A male subject, aged approximately 35 · a dermoscopic view of a skin lesion.
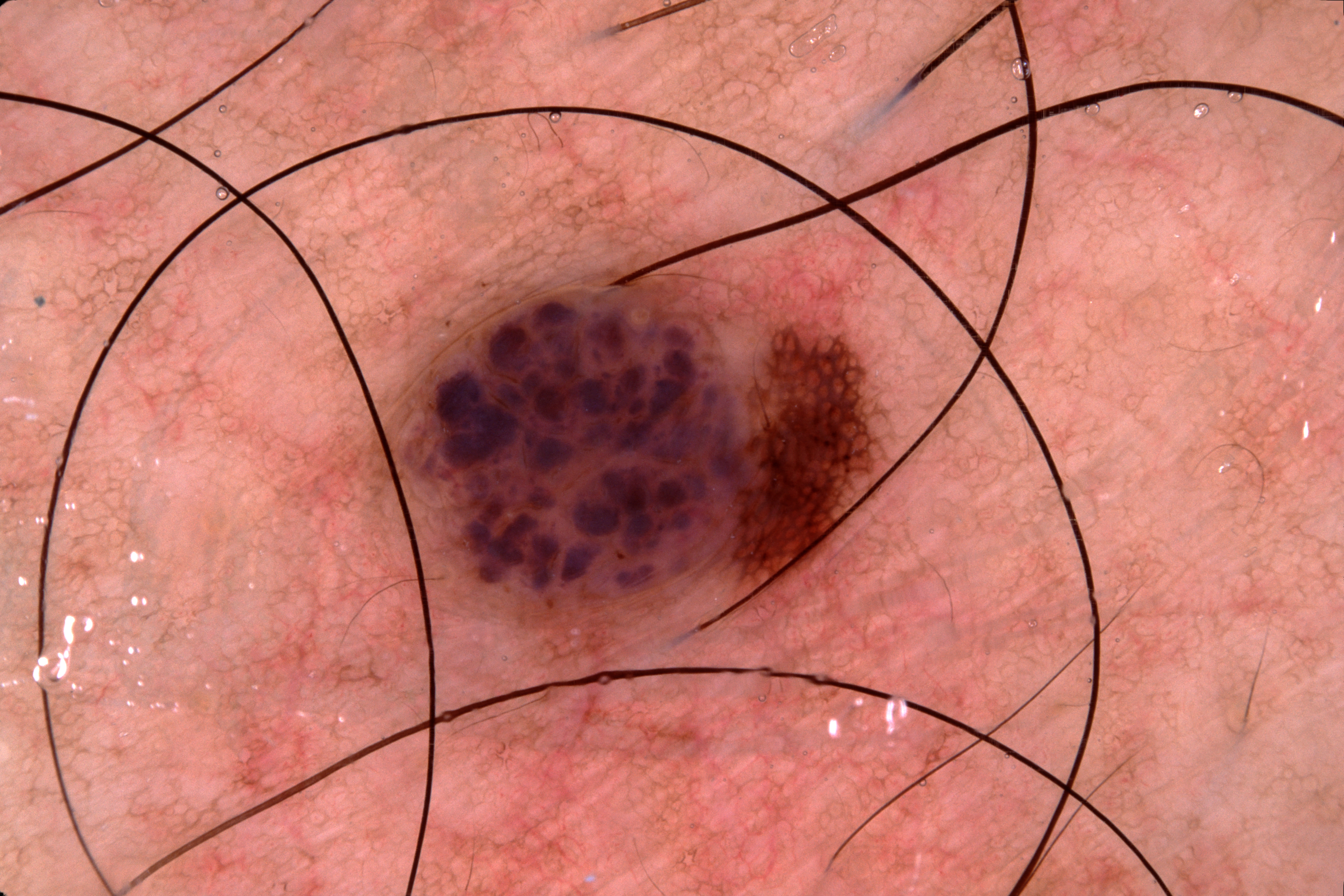Notes:
– lesion size · moderate
– location · left=359, top=230, right=906, bottom=654
– dermoscopic pattern · pigment network; absent: milia-like cysts, streaks, and negative network
– impression · a melanocytic nevus, a benign skin lesion